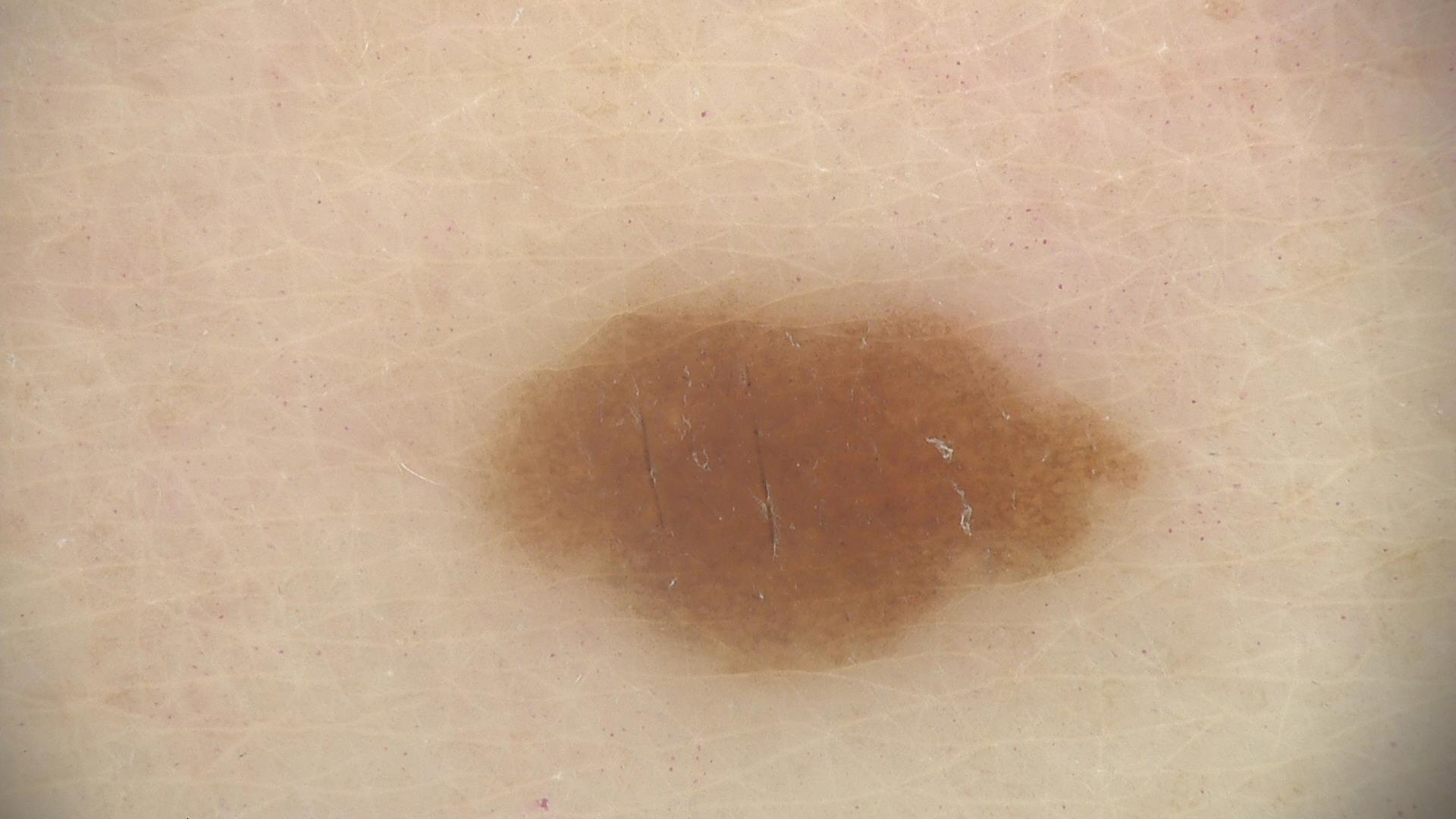Q: What is the diagnosis?
A: junctional nevus (expert consensus)